Close-up view · the lesion involves the back of the hand: 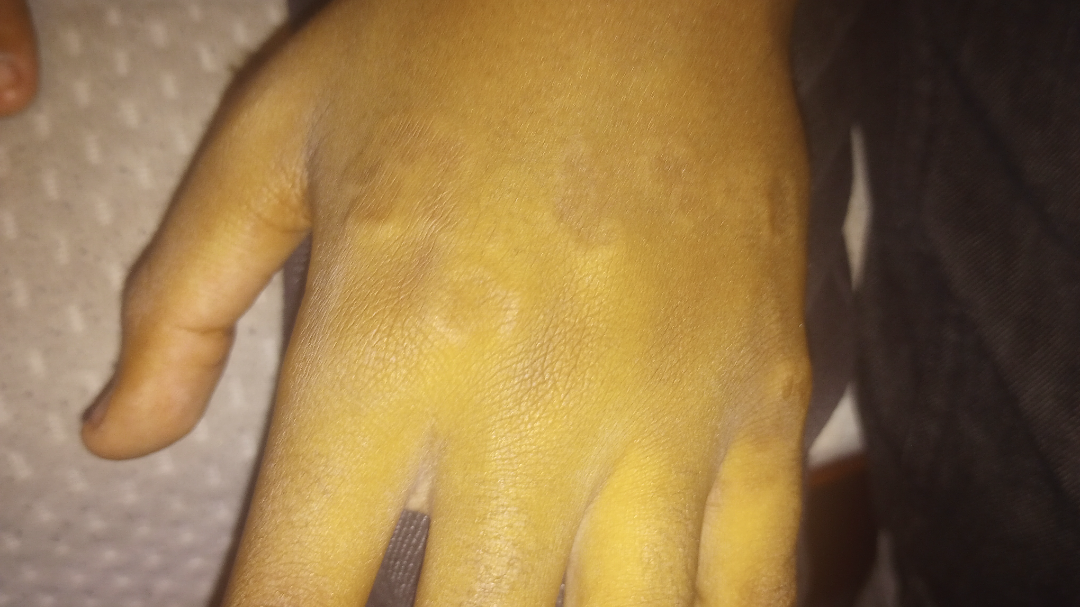assessment: indeterminate